A female patient roughly 55 years of age. Recorded as Fitzpatrick skin type II. Contact-polarized dermoscopy of a skin lesion — 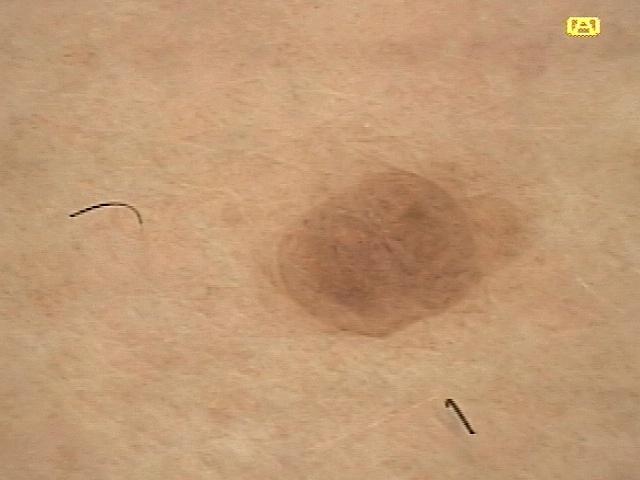Findings: The lesion is located on the trunk (the posterior trunk). Assessment: The diagnostic impression was a seborrheic keratosis.